A close-up photograph; the lesion involves the arm: 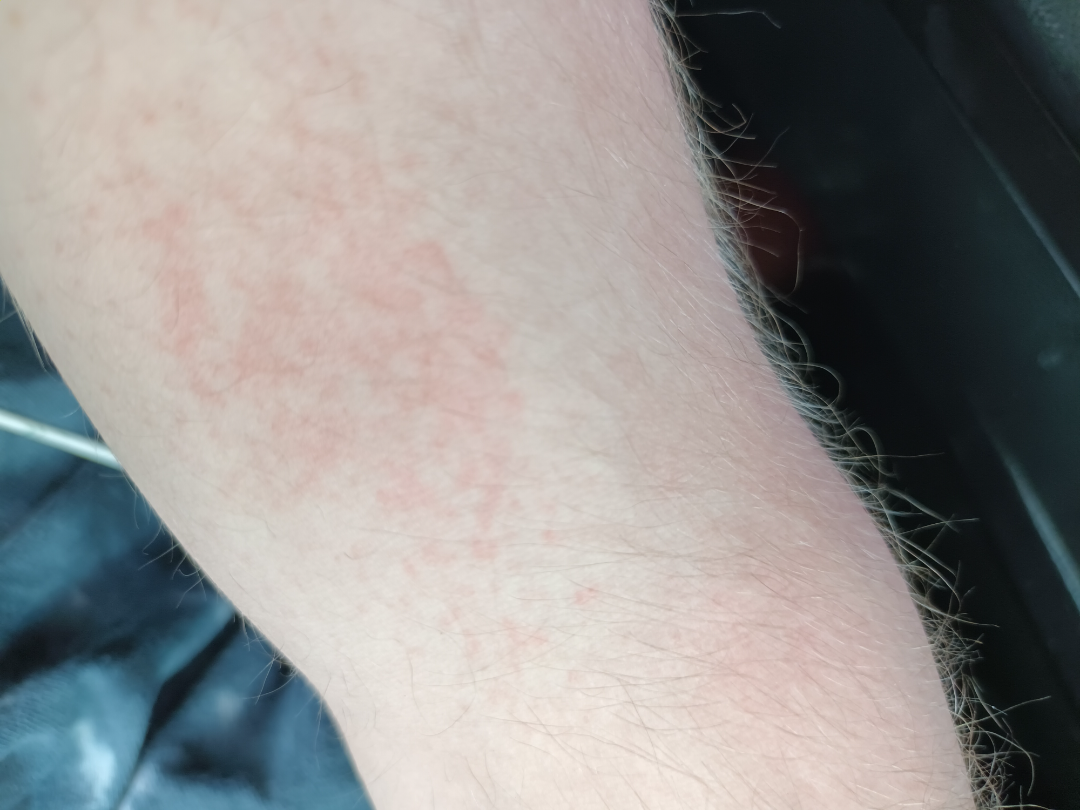assessment: unable to determine; described texture: flat; patient describes the issue as: a rash; other reported symptoms: none reported.